The photograph was taken at an angle · the patient is 50–59, female: 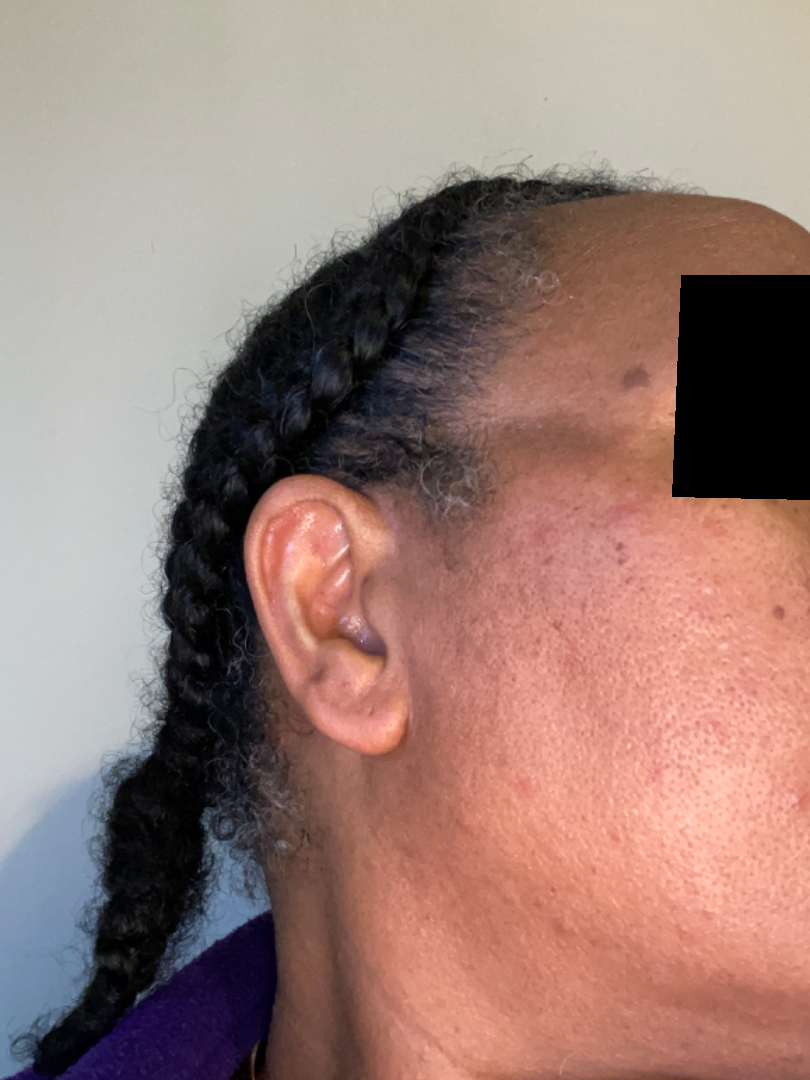Patient information: The patient notes the lesion is raised or bumpy. Symptoms reported: enlargement and bothersome appearance. Reported duration is about one day. The patient considered this a rash. No constitutional symptoms were reported. Review: The reviewing clinician's impression was: the differential, in no particular order, includes Acne and Rosacea.